The condition has been present for less than one week. Female subject, age 18–29. Reported lesion symptoms include itching, burning and bothersome appearance. A close-up photograph. The patient reports the lesion is flat and rough or flaky. Skin tone: Fitzpatrick skin type III; lay reviewers estimated Monk skin tone scale 3–4. The patient considered this a rash. The back of the hand is involved: 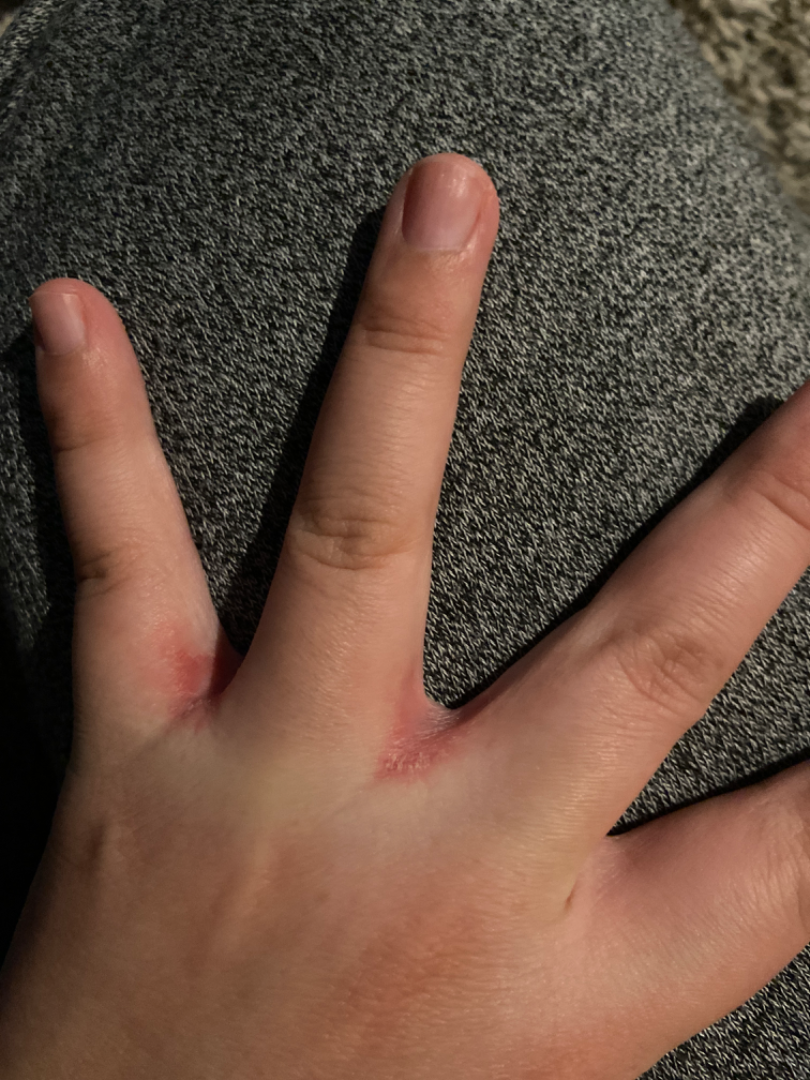<report>
  <differential>
    <leading>Intertrigo</leading>
    <considered>Psoriasis</considered>
    <unlikely>Scabies</unlikely>
  </differential>
</report>